The photograph was taken at an angle; the patient described the issue as a rash; the lesion is described as raised or bumpy; symptoms reported: pain, enlargement, itching and burning; the condition has been present for less than one week; the lesion involves the leg and arm; the patient indicates associated chills, fatigue and shortness of breath:
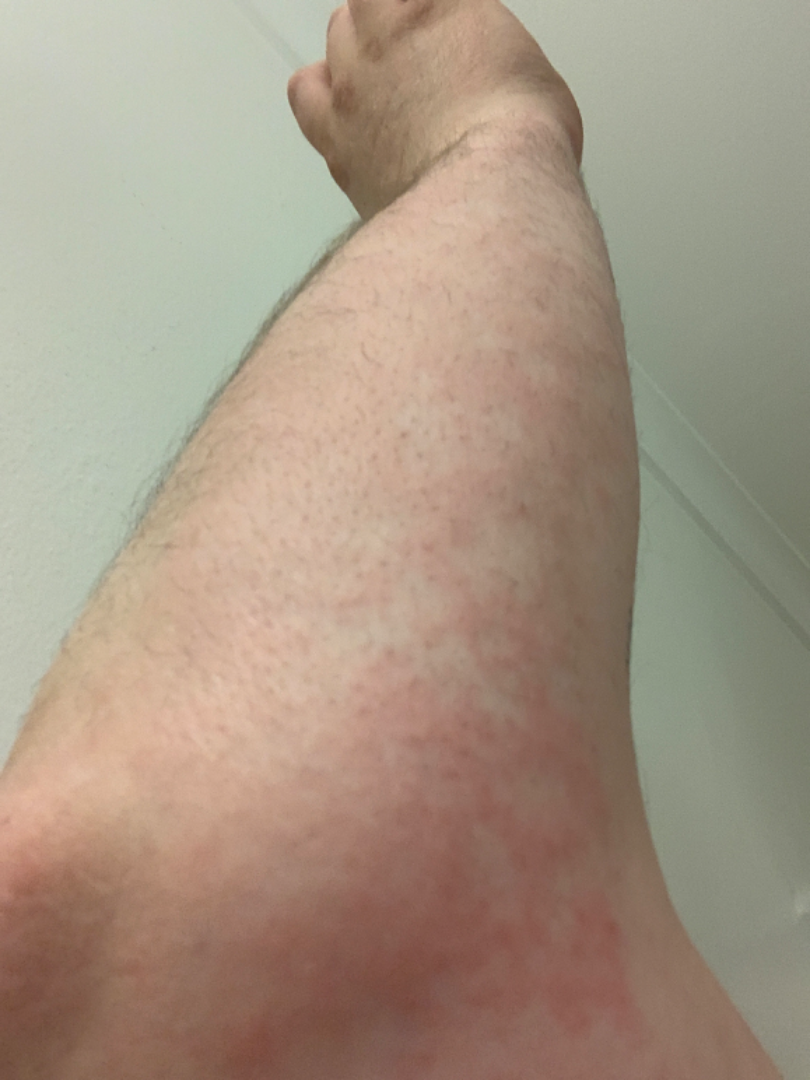assessment: not assessable.